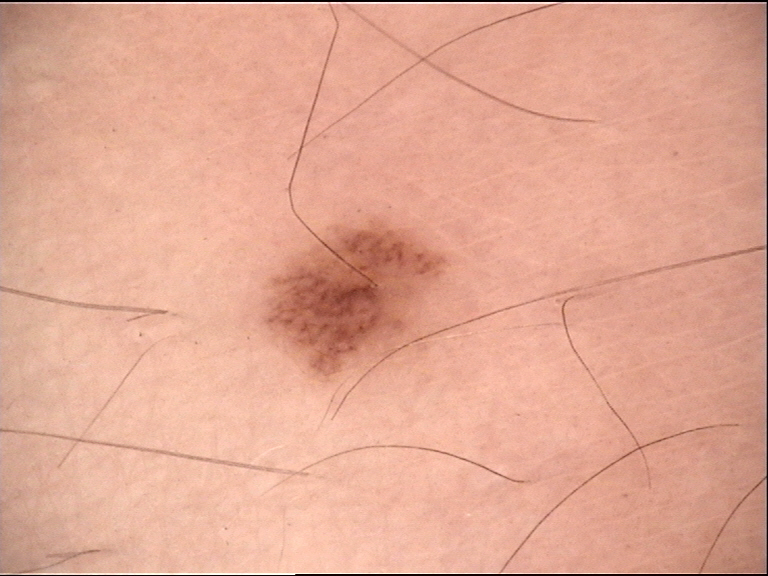Case:
* image · dermoscopy
* category · banal
* label · junctional nevus (expert consensus)